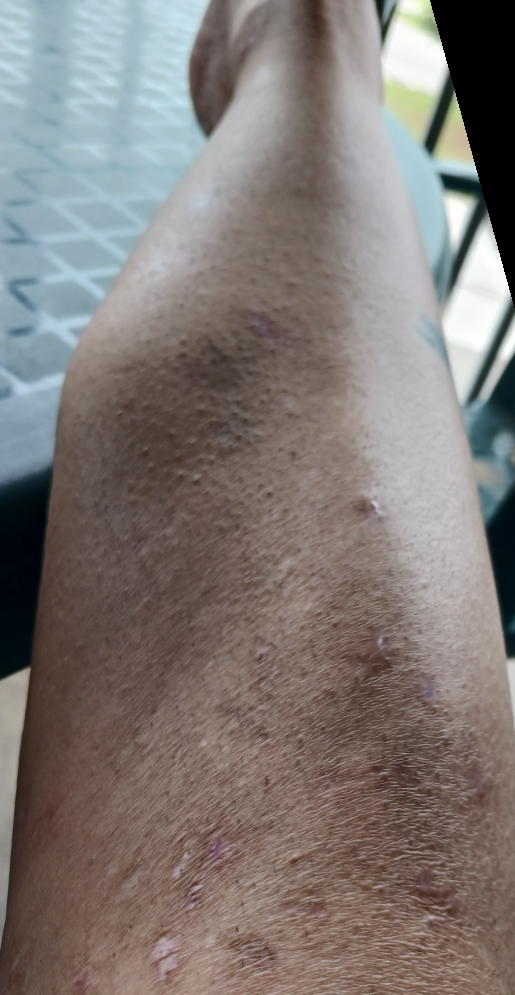The patient described the issue as a rash.
The lesion is described as raised or bumpy.
The lesion is associated with pain.
This image was taken at a distance.
Located on the leg.
The patient is a female aged 50–59.
Most likely Insect Bite; a remote consideration is Lichen Simplex Chronicus; less probable is Eczema; less likely is Acute dermatitis, NOS; lower on the differential is Erythema nodosum; a more distant consideration is Cutaneous sarcoidosis.